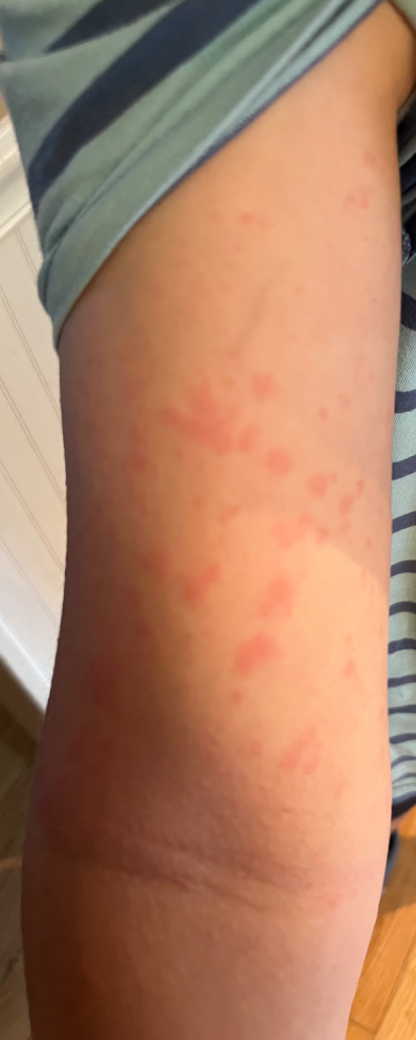The contributor is 40–49, female.
The back of the hand, arm and leg are involved.
The photograph is a close-up of the affected area.
One reviewing dermatologist: Insect Bite and Eczema were each considered, in no particular order; less likely is Urticaria.